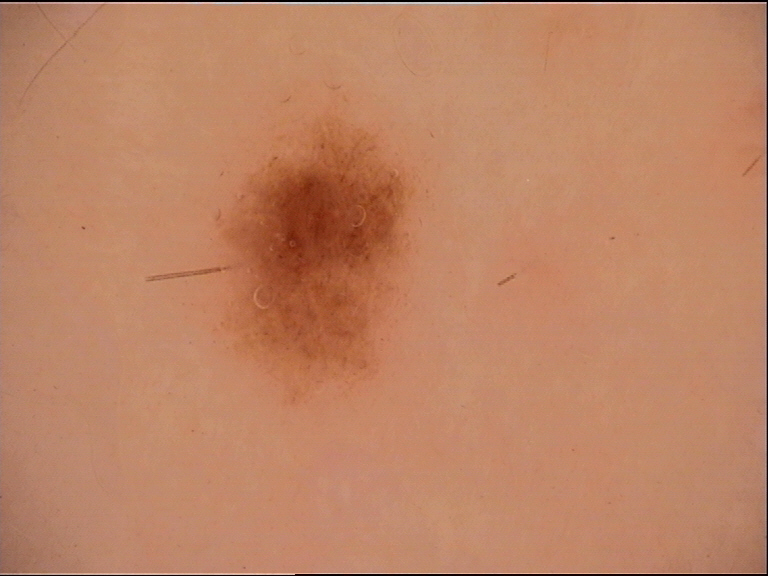A skin lesion imaged with a dermatoscope. Diagnosed as a dysplastic junctional nevus.